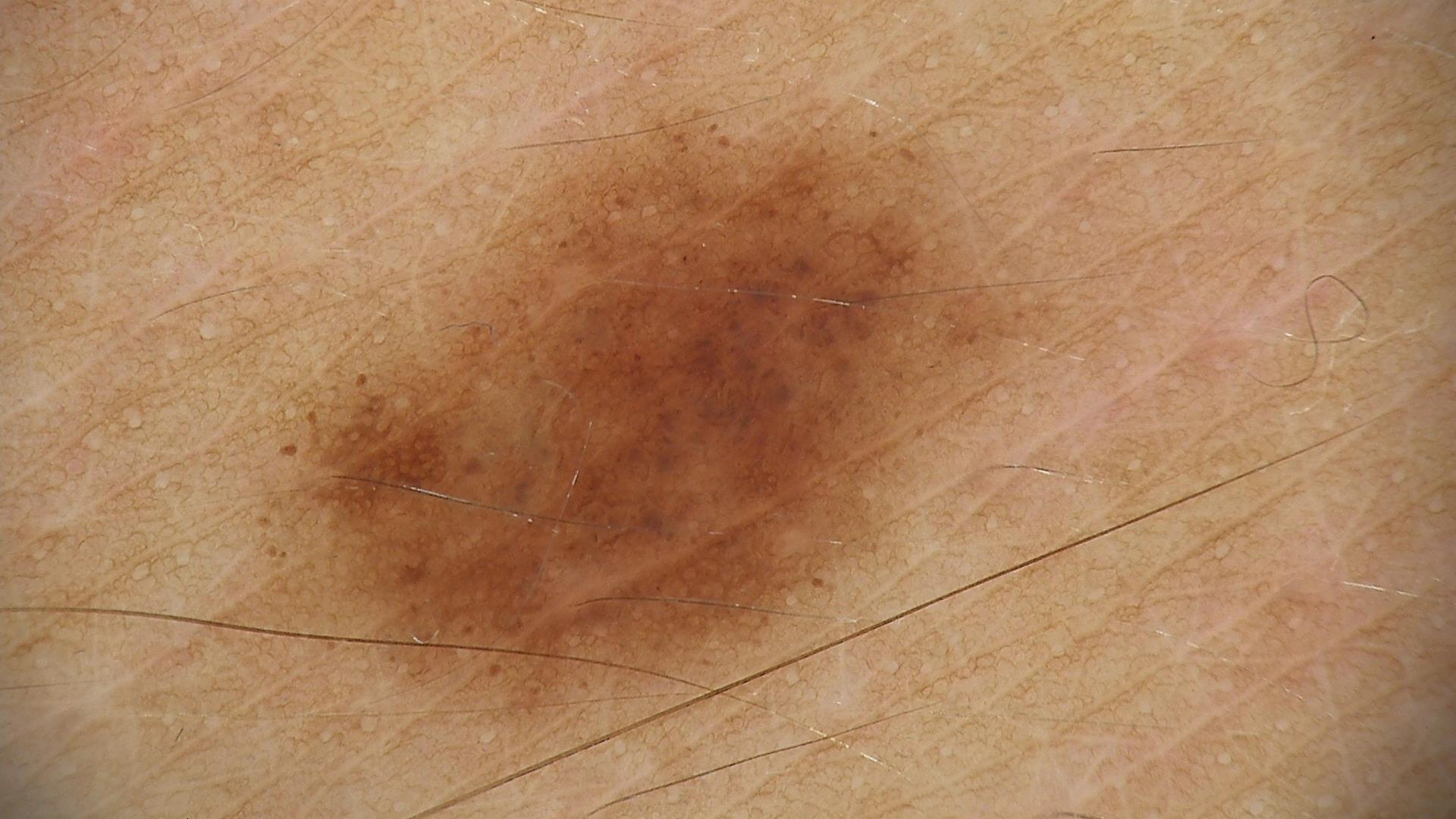Q: What is this lesion?
A: dysplastic junctional nevus (expert consensus)